A dermoscopic photograph of a skin lesion: 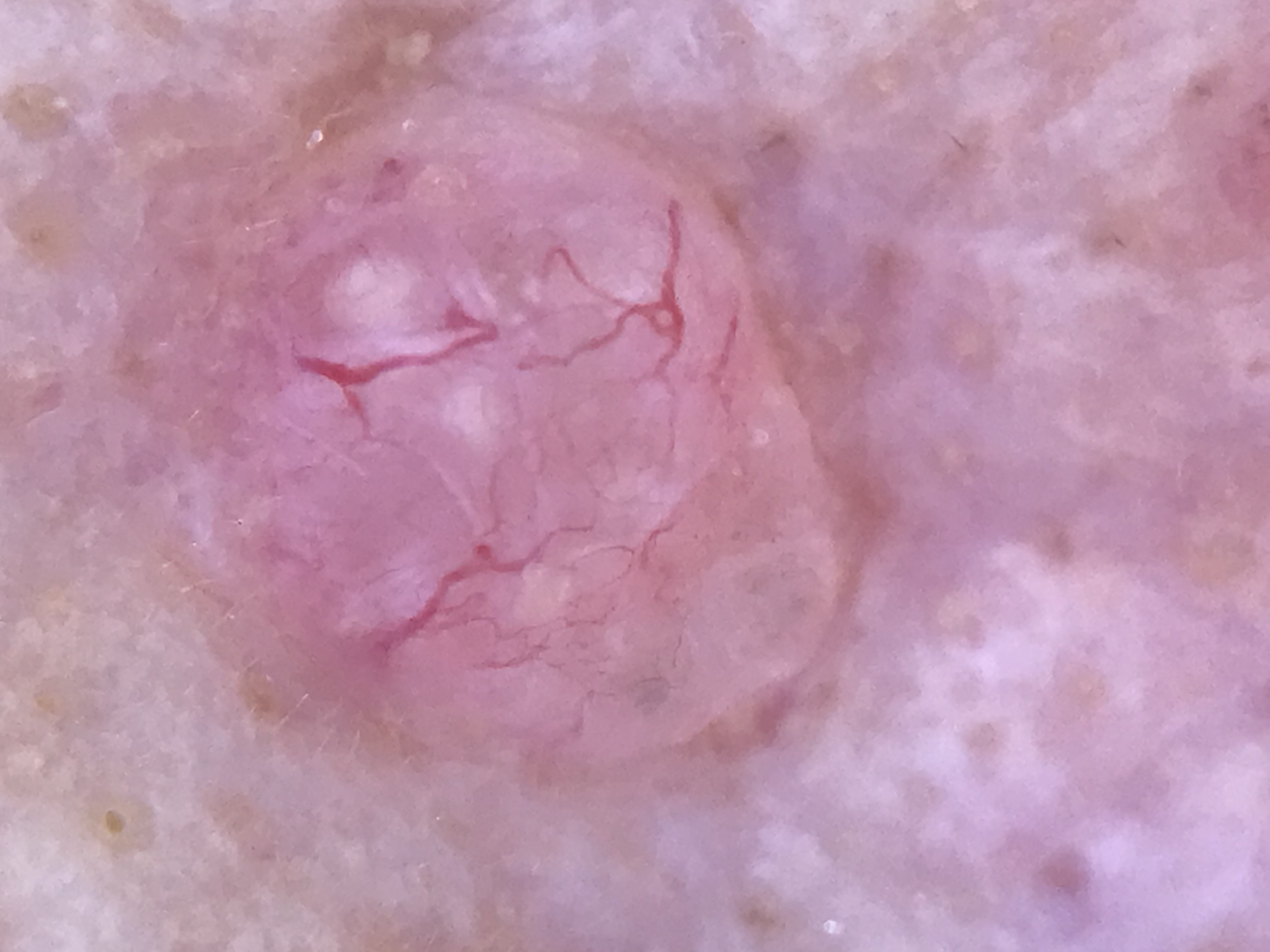The architecture is that of a keratinocytic lesion. Histopathology confirmed a basal cell carcinoma.